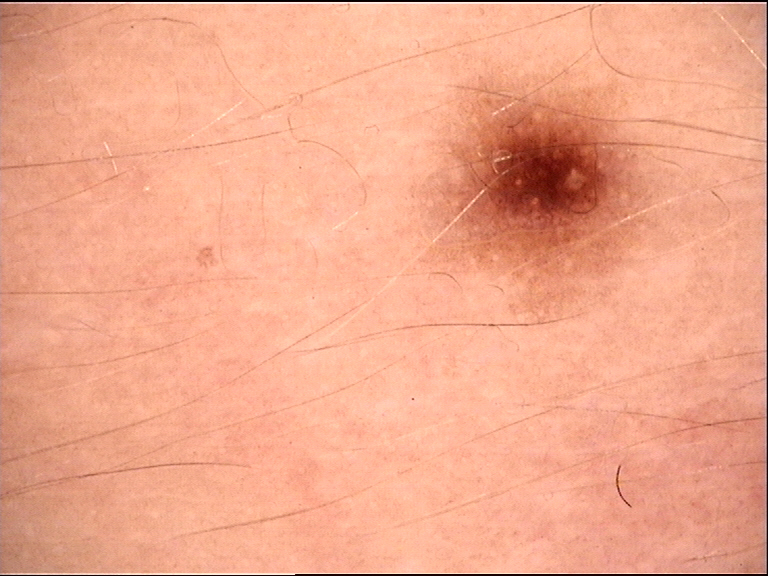class: junctional nevus (expert consensus).